A dermatoscopic image of a skin lesion:
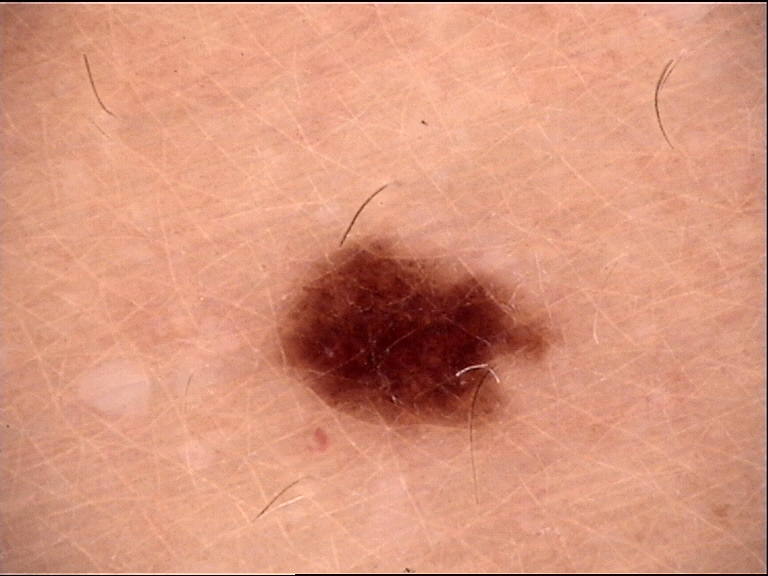| field | value |
|---|---|
| assessment | dysplastic junctional nevus (expert consensus) |